This is a close-up image; the contributor notes itching and bothersome appearance; the affected area is the arm and leg; non-clinician graders estimated Monk Skin Tone 5 or 6; the patient described the issue as a rash; present for less than one week.
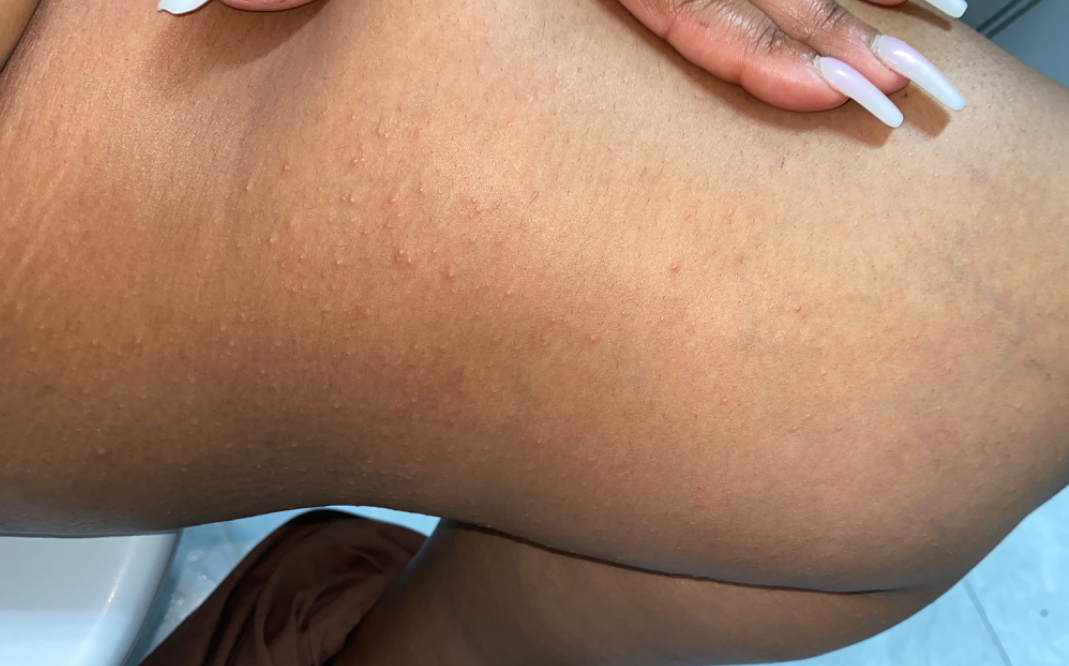Review: Favoring Folliculitis; with consideration of Keratosis pilaris.